A clinical photo of a skin lesion taken with a smartphone; a patient in their mid-70s:
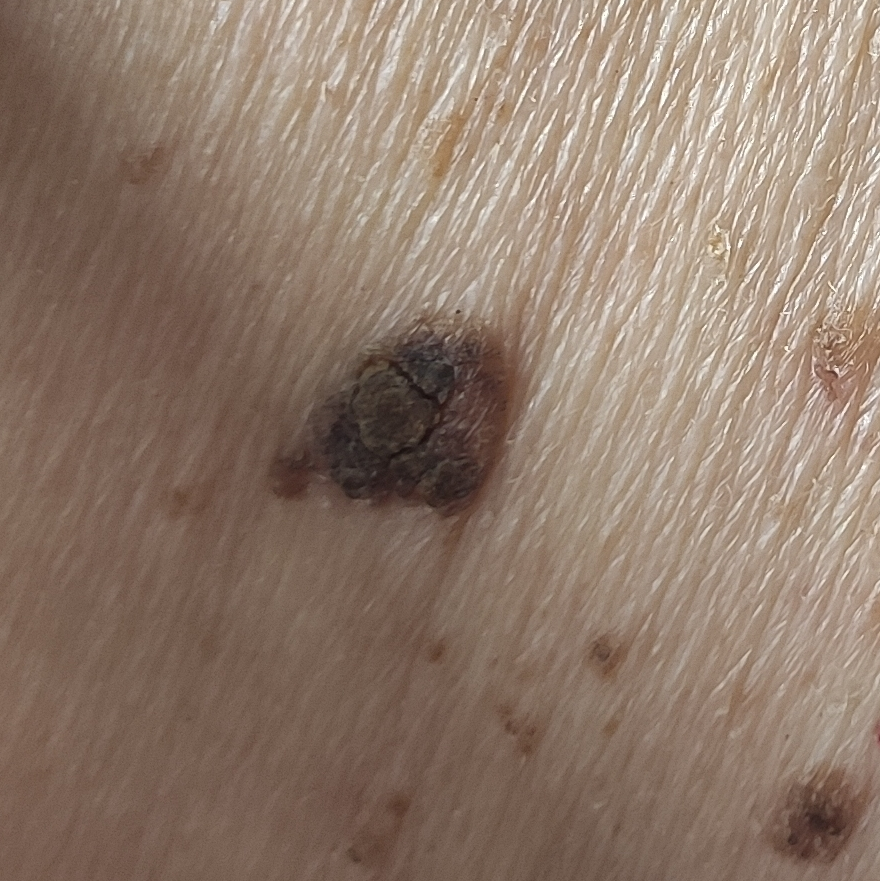Clinical context:
Per patient report, the lesion is elevated, has grown, itches, has bled, and has changed.
Conclusion:
The clinical impression was a seborrheic keratosis.